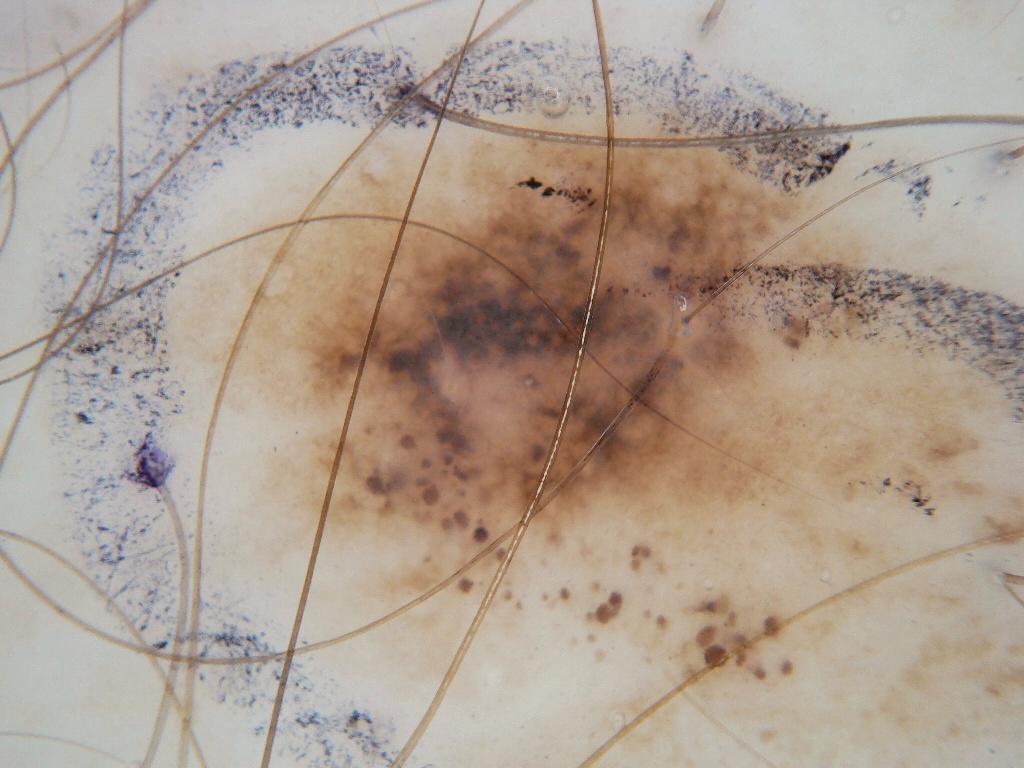A male patient in their 60s.
A dermoscopic close-up of a skin lesion.
On dermoscopy, the lesion shows globules; no milia-like cysts, streaks, pigment network, or negative network.
As (left, top, right, bottom), the visible lesion spans <box>149, 88, 1021, 766</box>.
A large lesion occupying much of the field.
Clinically diagnosed as a melanocytic nevus.